A dermoscopic close-up of a skin lesion: 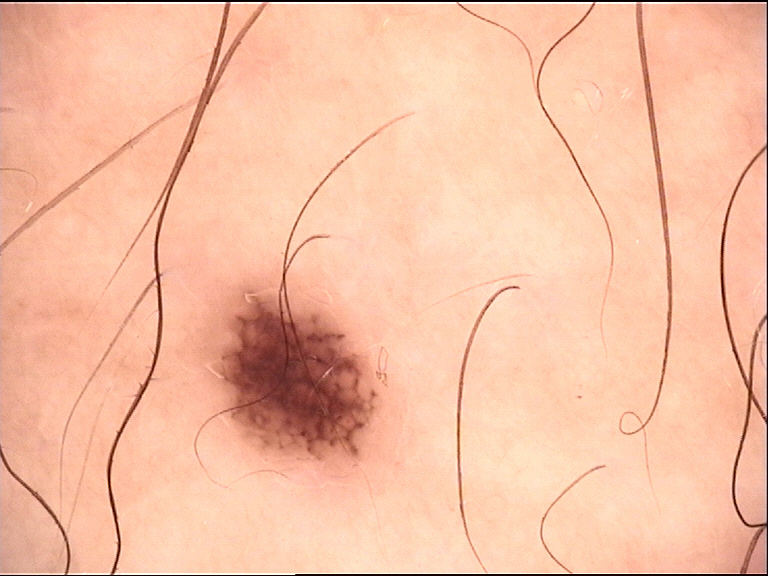category: banal | assessment: junctional nevus (expert consensus).